A smartphone photograph of a skin lesion — 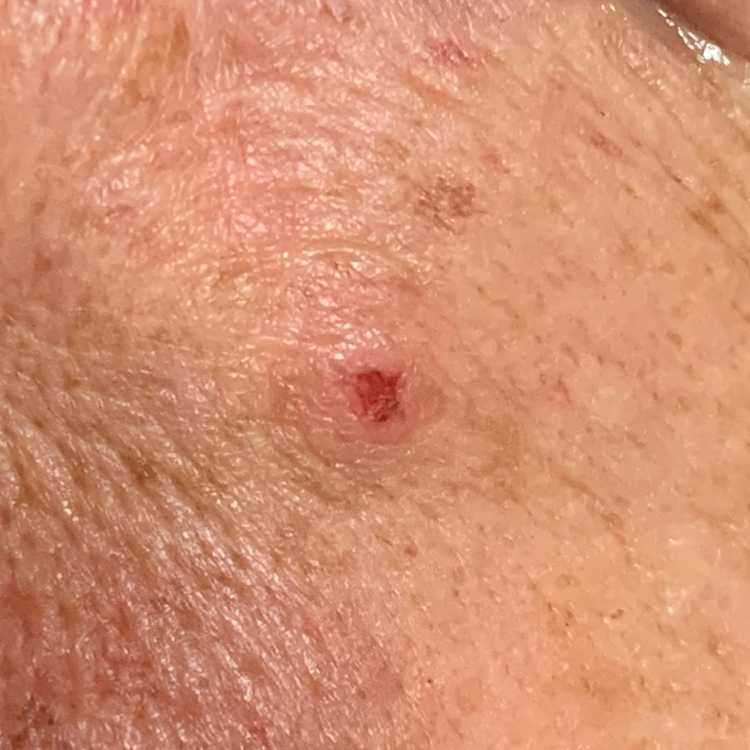Summary:
By the patient's account, the lesion has bled and is elevated, but does not itch.
Conclusion:
Histopathology confirmed a malignant skin lesion — a basal cell carcinoma.